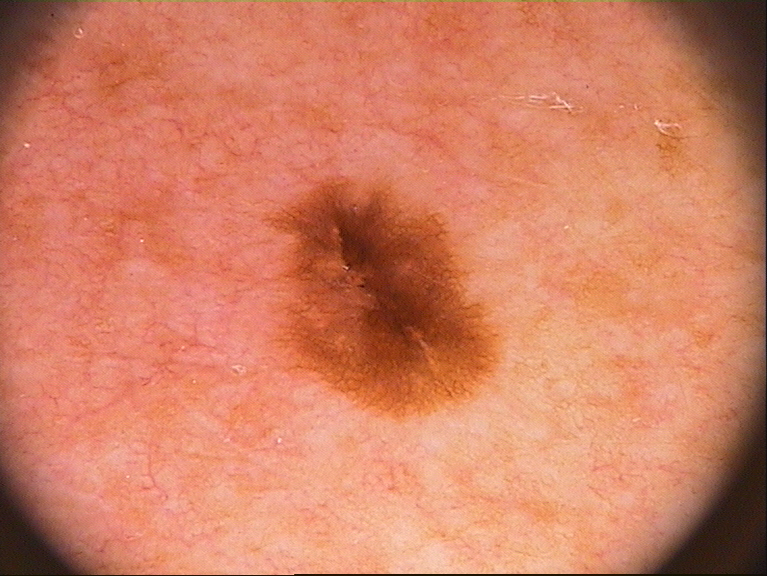<record>
<image>
  <modality>dermoscopy</modality>
</image>
<lesion_location>
  <bbox_xyxy>258, 165, 503, 424</bbox_xyxy>
</lesion_location>
<dermoscopic_features>
  <present>pigment network</present>
  <absent>negative network, globules, streaks, milia-like cysts</absent>
</dermoscopic_features>
<diagnosis>
  <name>melanocytic nevus</name>
  <malignancy>benign</malignancy>
  <lineage>melanocytic</lineage>
  <provenance>clinical</provenance>
</diagnosis>
</record>